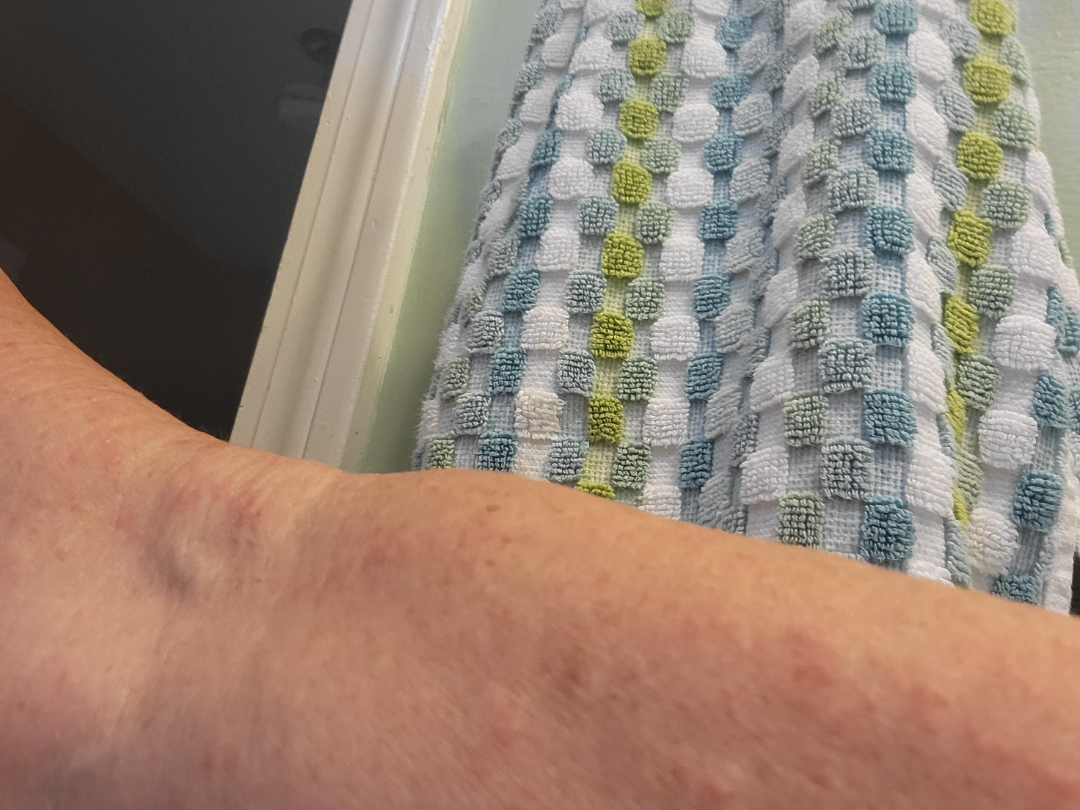The case was indeterminate on photographic review. The lesion involves the arm, head or neck and front of the torso. This is a close-up image. Symptoms reported: burning, bothersome appearance and itching. Female contributor, age 60–69. Skin tone: Fitzpatrick I; lay graders estimated Monk skin tone scale 2–3.